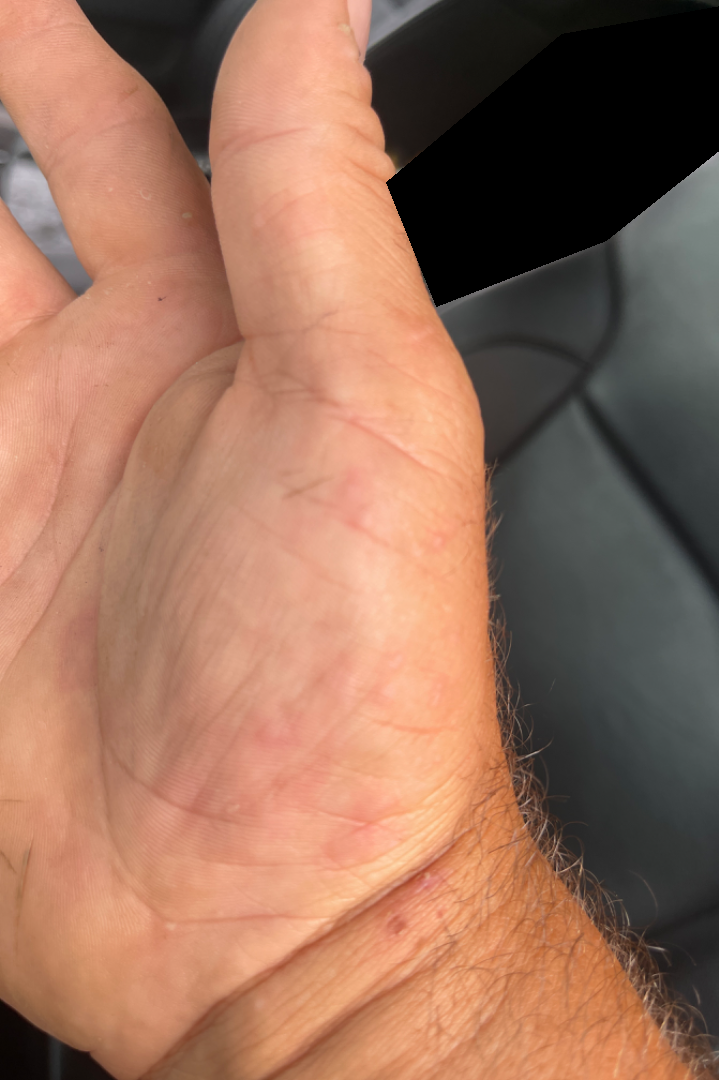Patient information: This is a close-up image. Review: On photographic review: most consistent with Eczema.